A dermoscopic image of a skin lesion:
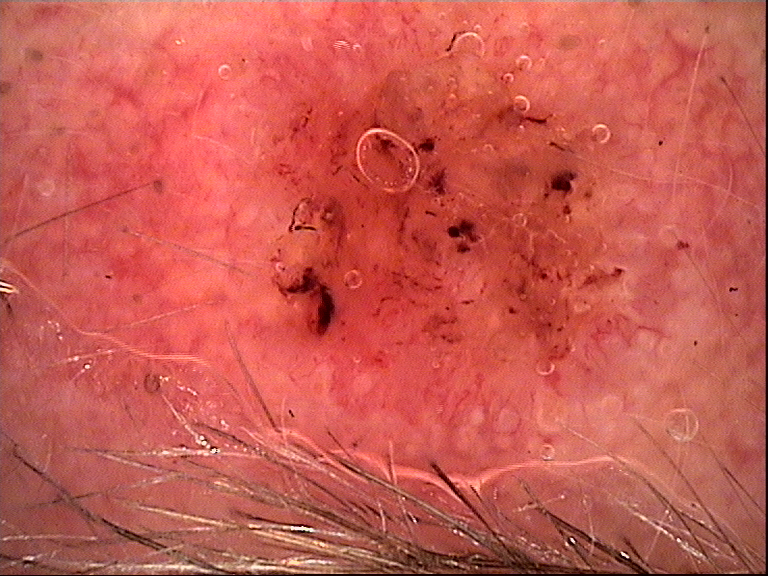Confirmed on histopathology as a keratinocytic, malignant lesion — a squamous cell carcinoma.